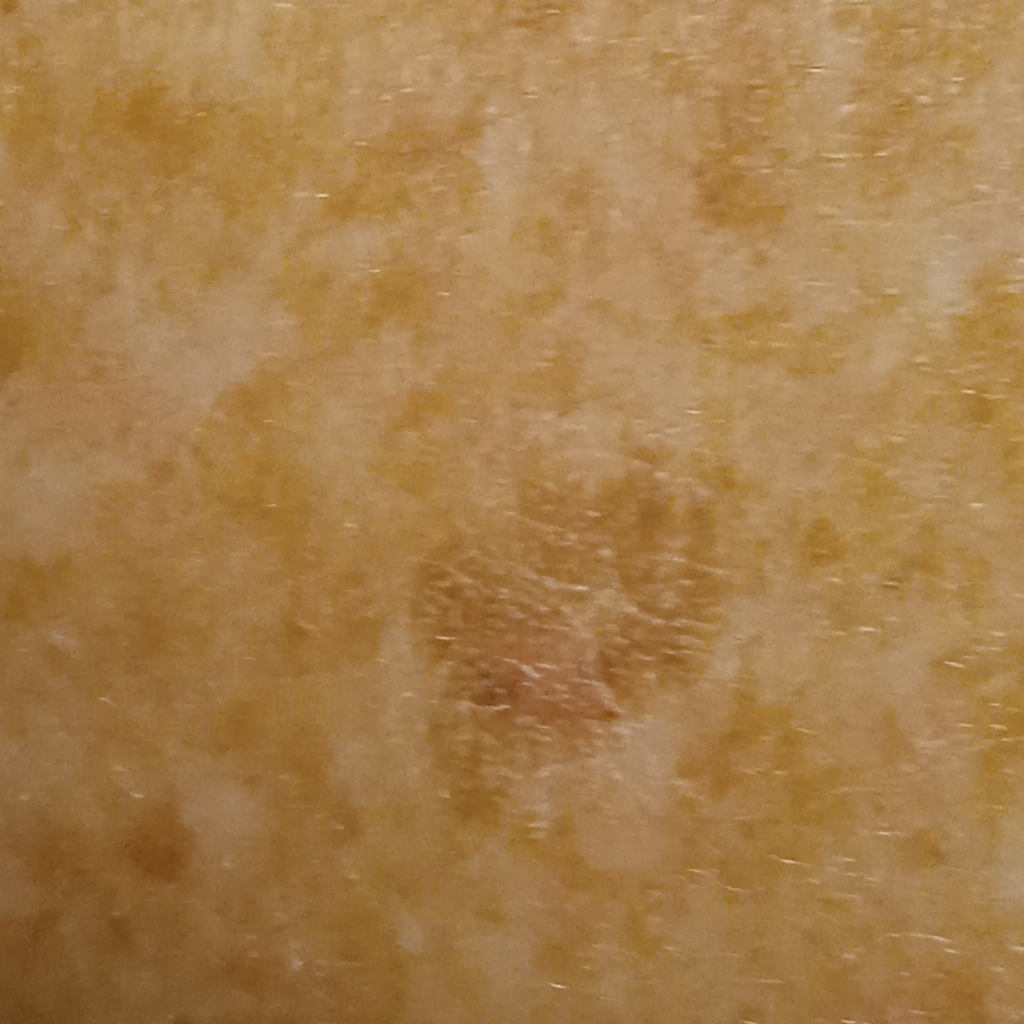By self-report, a personal history of cancer and no prior organ transplant.
Acquired for a research image collection, with no referral diagnosis.
A male patient 73 years old.
The patient describes having numerous moles.
The patient says their skin reddens with sun exposure.
The lesion is on the back.
The diagnostic impression was a seborrheic keratosis.